The patient was assessed as Fitzpatrick phototype III · a male patient aged approximately 85 or older — 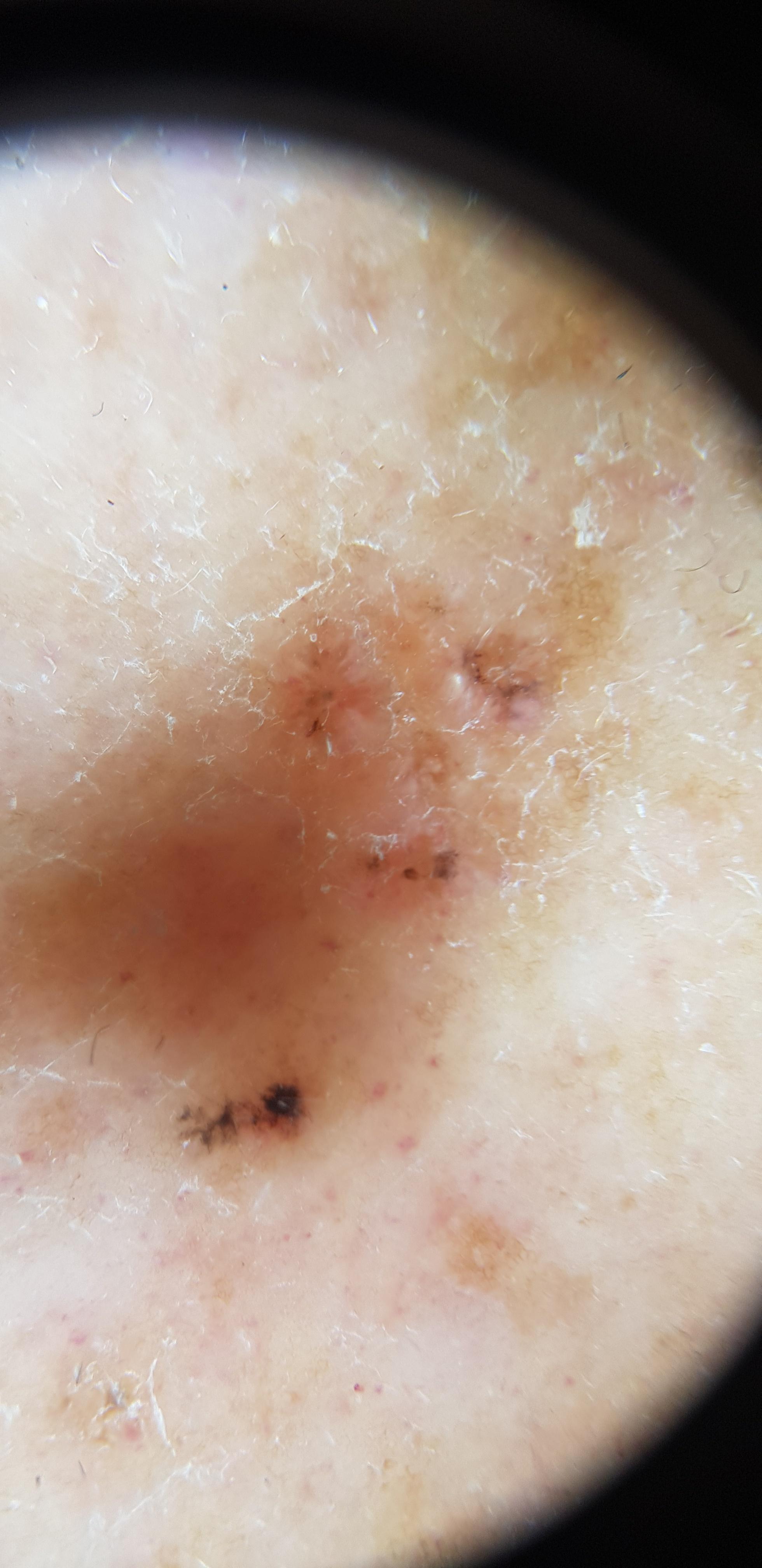Located on a lower extremity. Confirmed on histopathology as a malignant, adnexal lesion — a basal cell carcinoma.